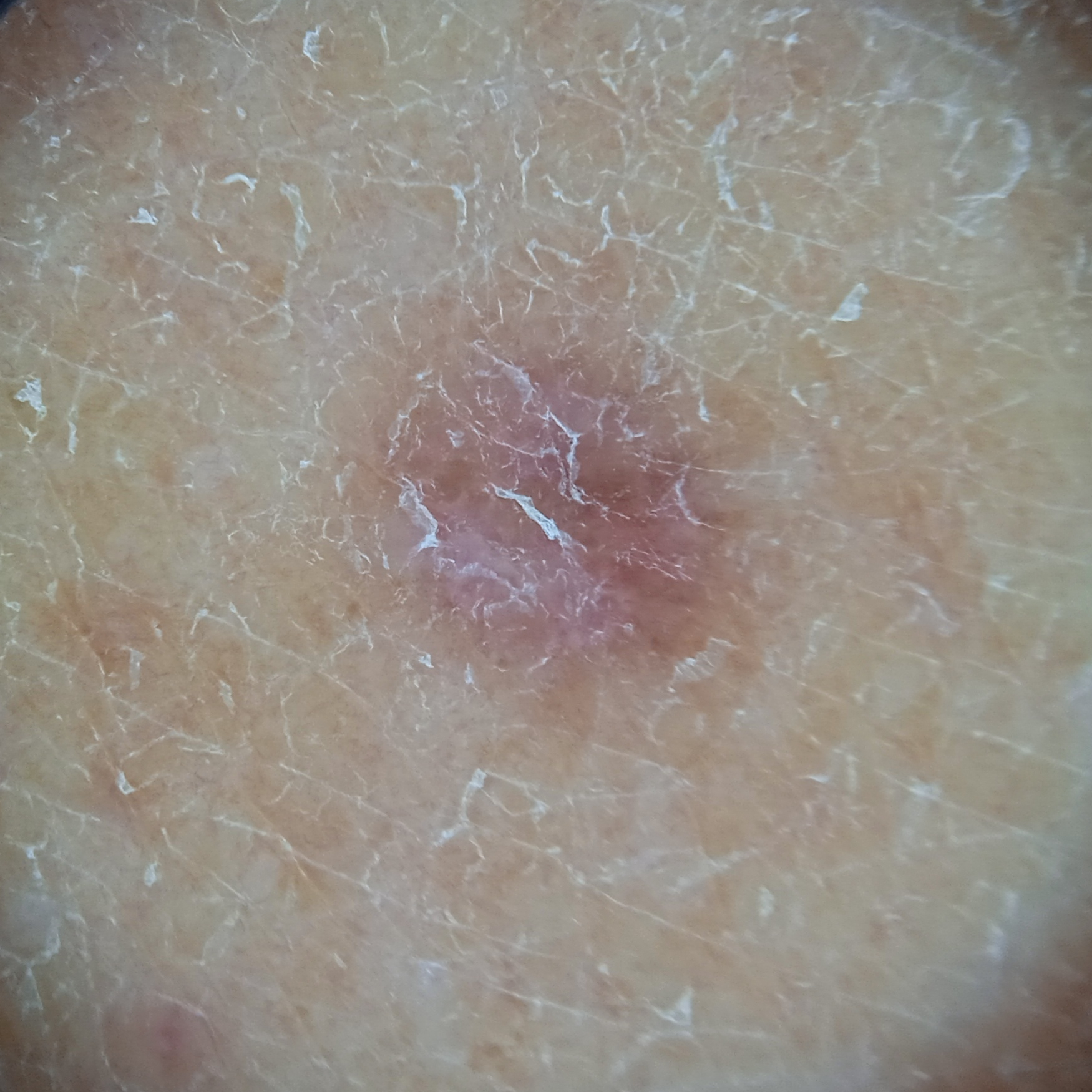Q: Why was this imaged?
A: research study (no referral diagnosis)
Q: How does the patient's skin react to sun?
A: skin tans without first burning
Q: What are the relevant risk factors?
A: a family history of skin cancer, a personal history of cancer, a personal history of skin cancer
Q: What kind of image is this?
A: dermoscopy
Q: Lesion size?
A: 5.2 mm
Q: What was the diagnosis?
A: dermatofibroma (dermatologist consensus)